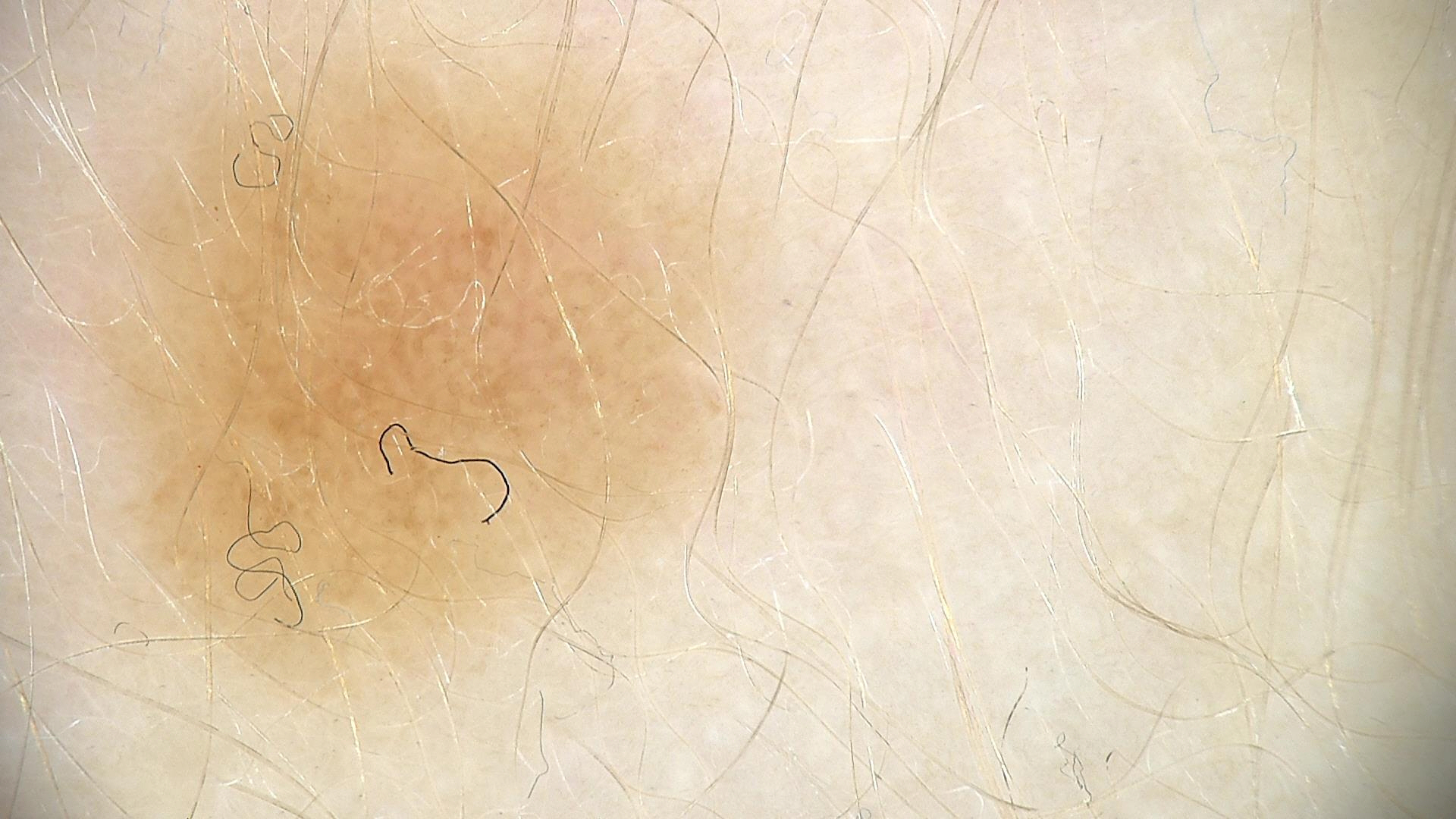• diagnostic label · dysplastic junctional nevus (expert consensus)